A dermoscopy image of a single skin lesion.
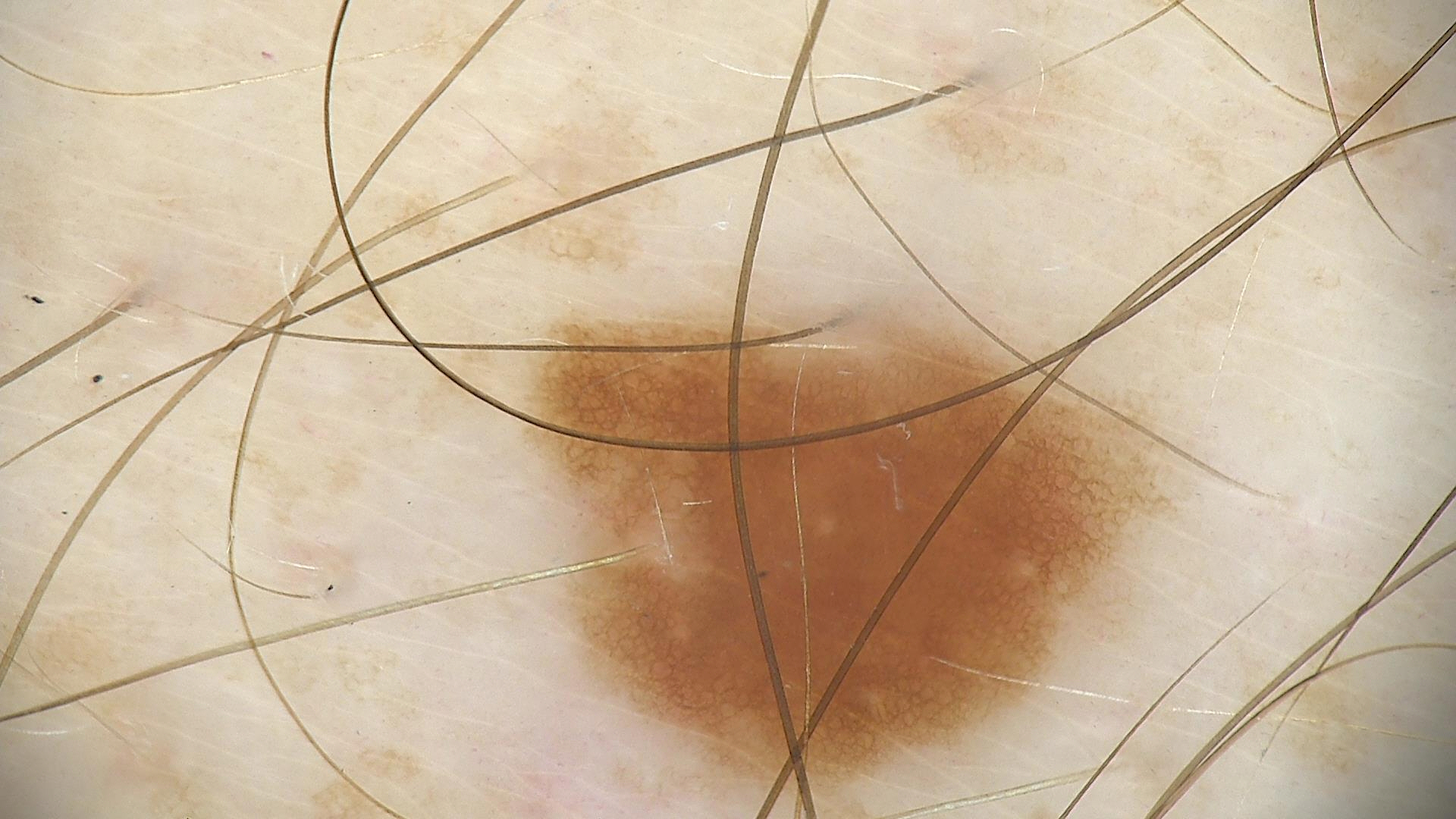Consistent with a dysplastic junctional nevus.